The patient describes having a moderate number of moles · the patient says their skin tans without first burning · a female patient age 75 · imaged for a research study, with no referral diagnosis recorded · a clinical photograph showing a skin lesion: 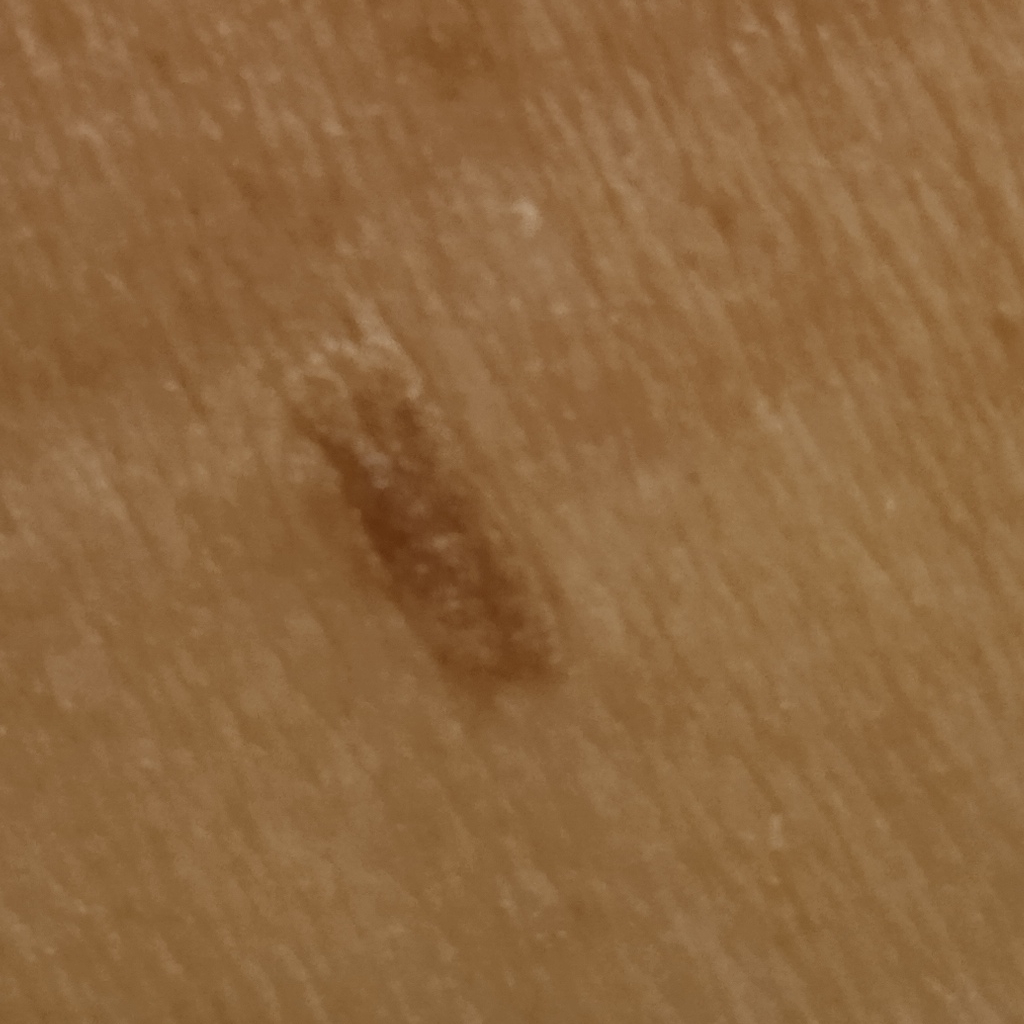{
  "lesion_location": "the back",
  "lesion_size": {
    "diameter_mm": 8.4
  },
  "diagnosis": {
    "name": "seborrheic keratosis",
    "malignancy": "benign"
  }
}